A dermoscopic close-up of a skin lesion: 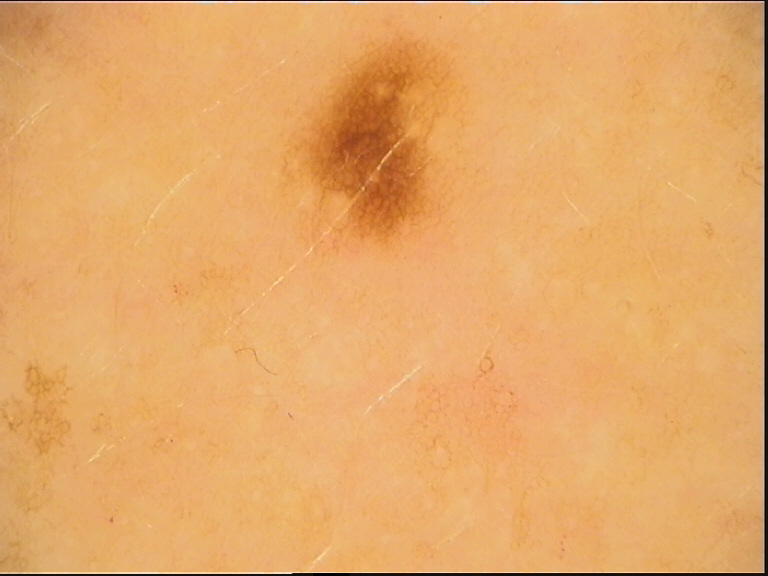classification: banal; label: junctional nevus (expert consensus).